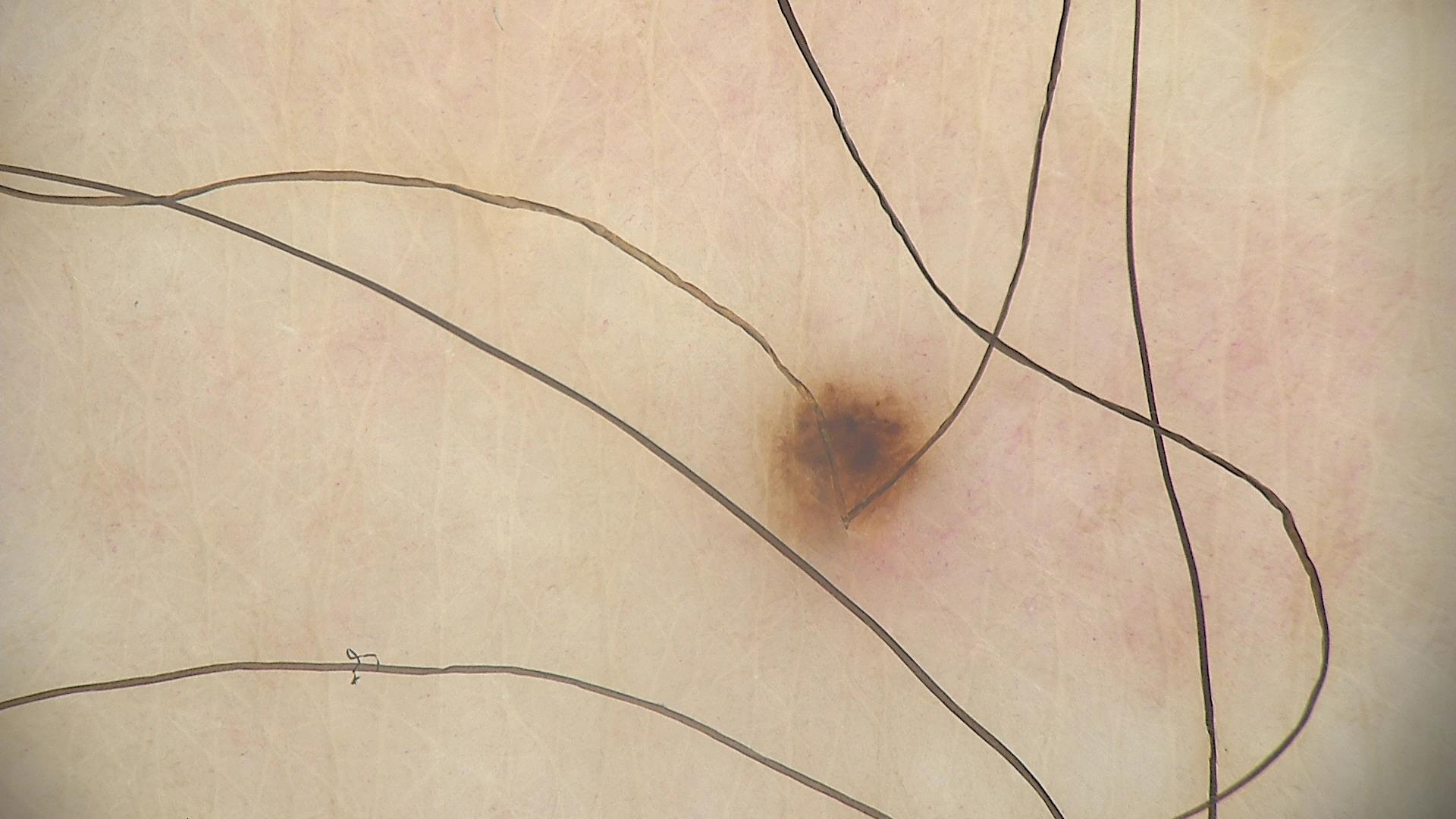A dermoscopic photograph of a skin lesion. The diagnosis was a dysplastic junctional nevus.